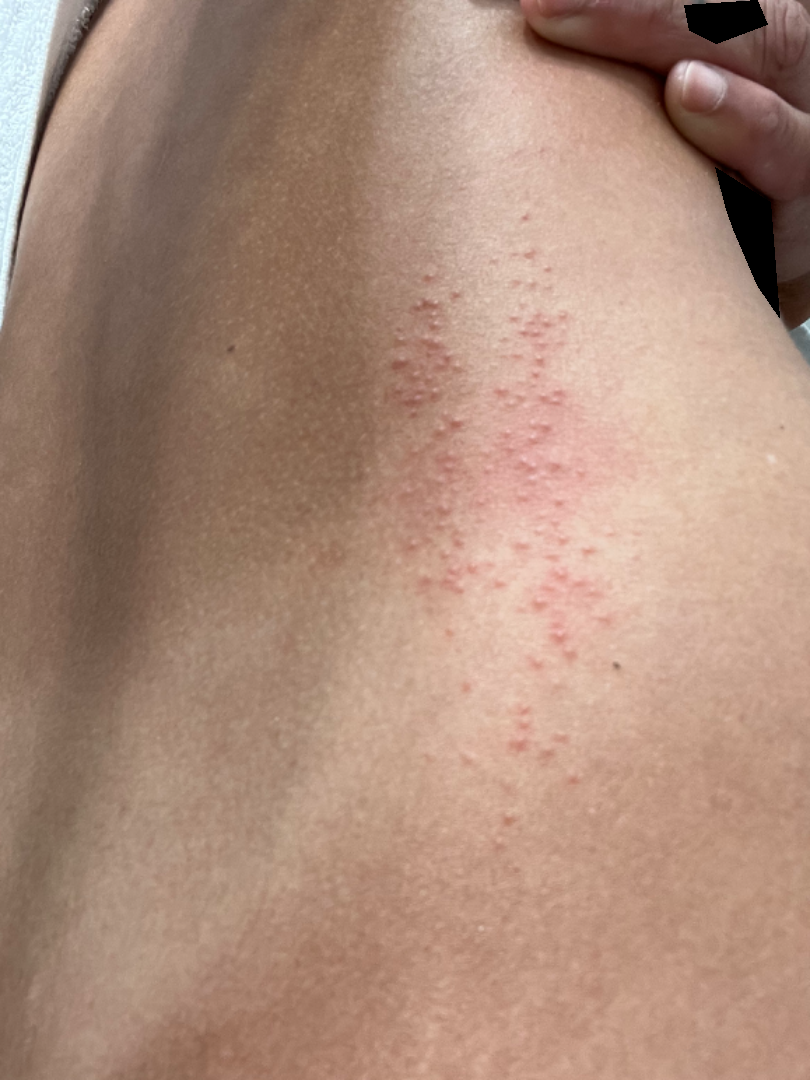lesion texture: raised or bumpy | symptom duration: less than one week | self-categorized as: a rash | image framing: close-up | patient: female, age 18–29 | constitutional symptoms: joint pain, fatigue and shortness of breath | skin tone: FST III; lay reviewers estimated MST 5 (US pool) or 4 (India pool) | anatomic site: back of the torso | differential: most consistent with Miliaria; also raised was Milia; a remote consideration is Eczema.